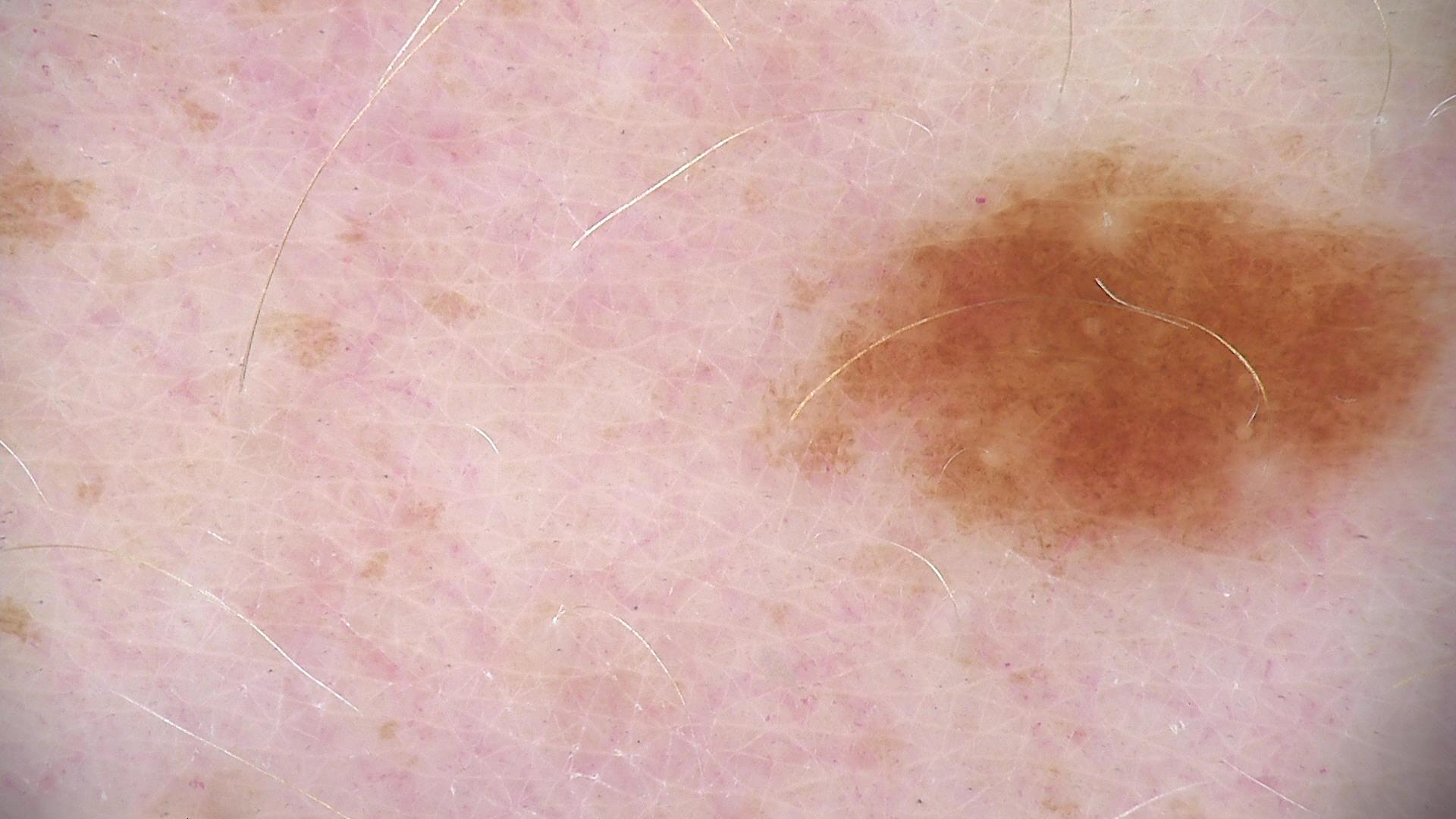Consistent with a benign lesion — a dysplastic junctional nevus.